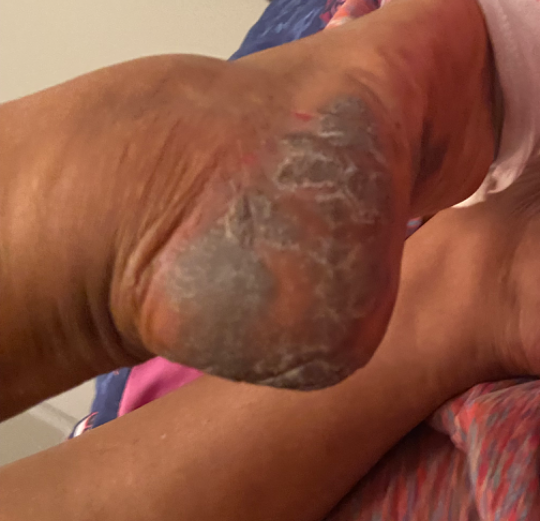The case was indeterminate on photographic review. Located on the palm, top or side of the foot and leg. The patient indicates the lesion is rough or flaky. Reported lesion symptoms include itching, enlargement, pain, bothersome appearance and darkening. Present for more than one year. The photograph is a close-up of the affected area. Skin tone: Fitzpatrick VI; lay reviewers estimated MST 6 (US pool) or 4 (India pool).